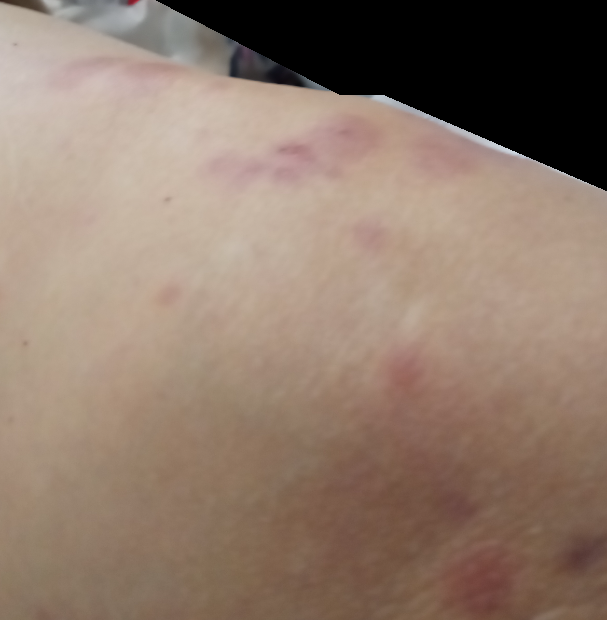The skin condition could not be confidently assessed from this image. The affected area is the front of the torso, leg and top or side of the foot. The patient is a female aged 60–69. An image taken at an angle.